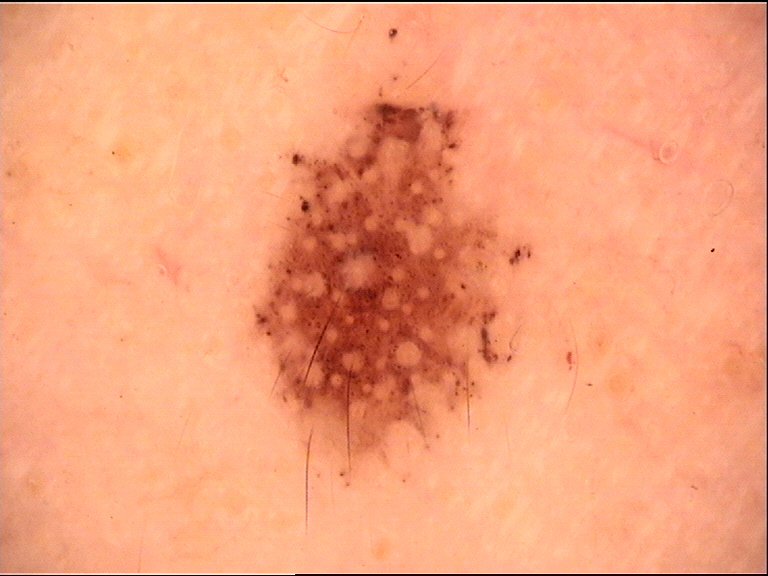label — dysplastic junctional nevus (expert consensus).